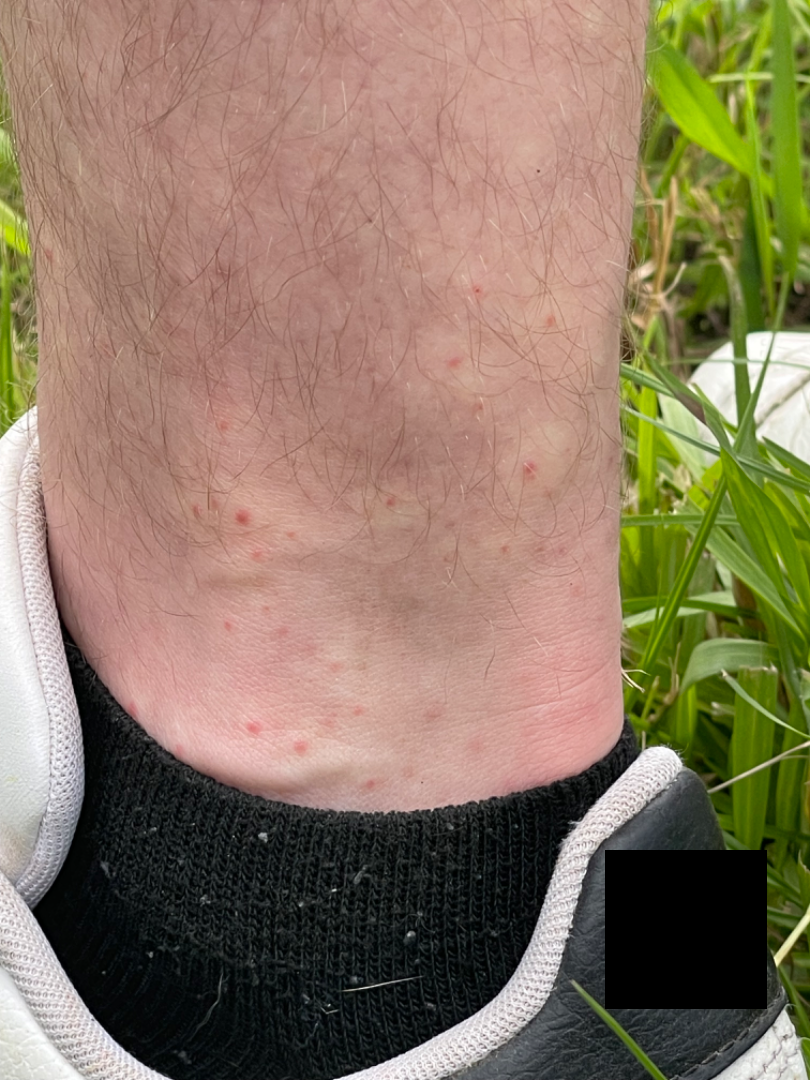The impression was split between Insect Bite and petechiae.